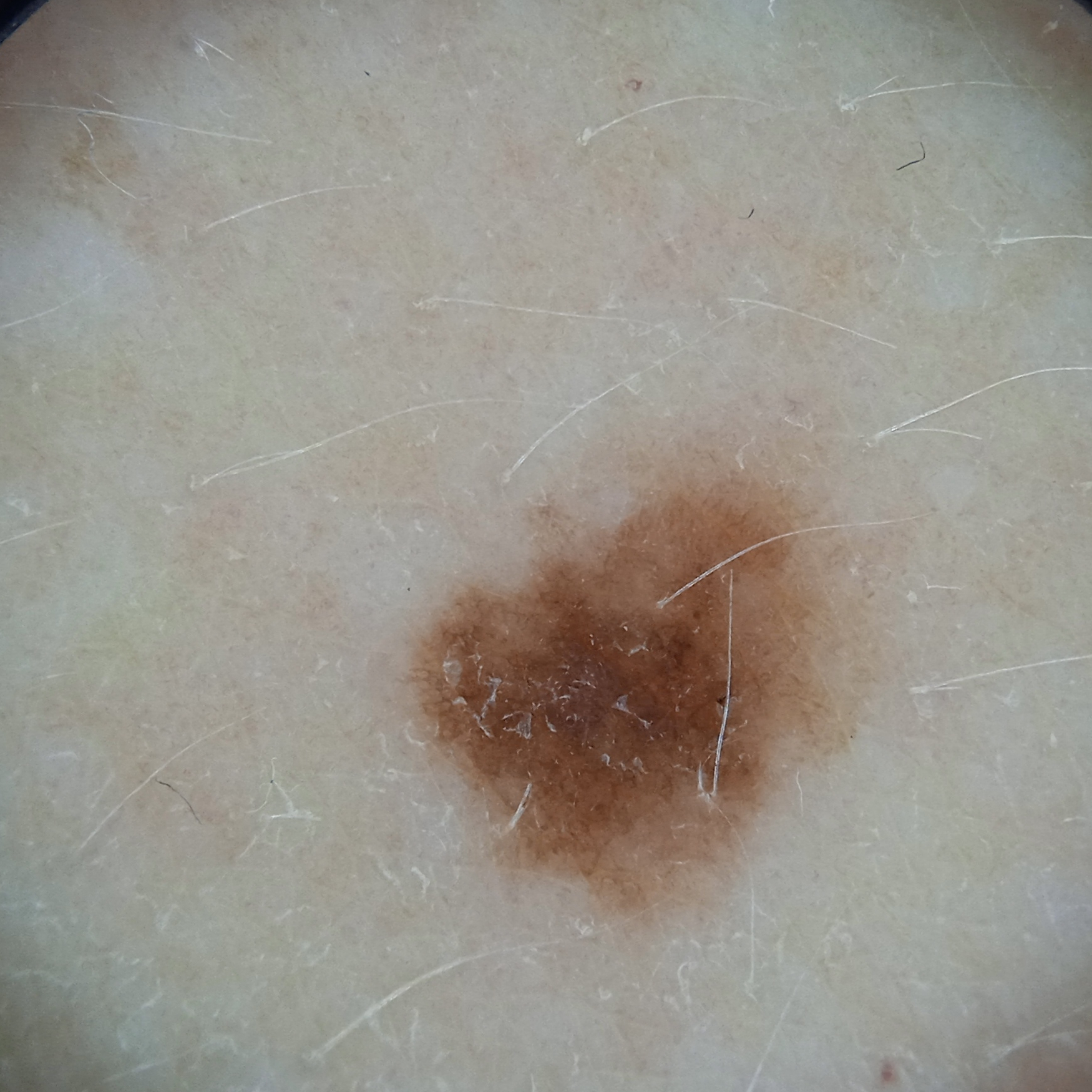A dermoscopic image of a skin lesion. A female subject age 50. A moderate number of moles by the patient's own estimate. Imaged for a research study, with no referral diagnosis recorded. The patient reports a personal history of skin cancer. The patient says their skin reddens with sun exposure. The lesion is located on the torso. The lesion measures approximately 5.4 mm. The diagnostic impression was a melanocytic nevus.